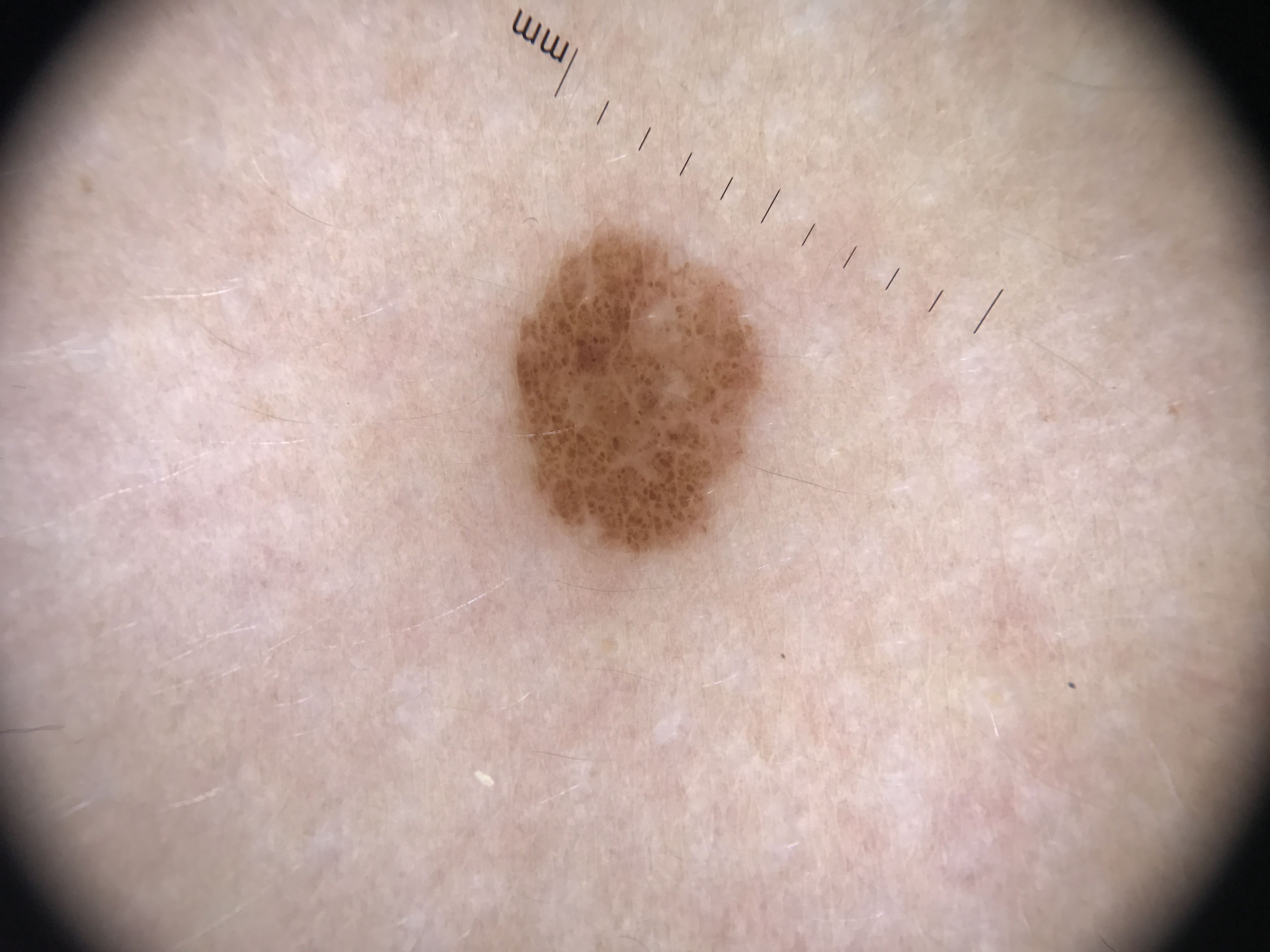image: dermoscopy; diagnostic label: compound nevus (expert consensus).